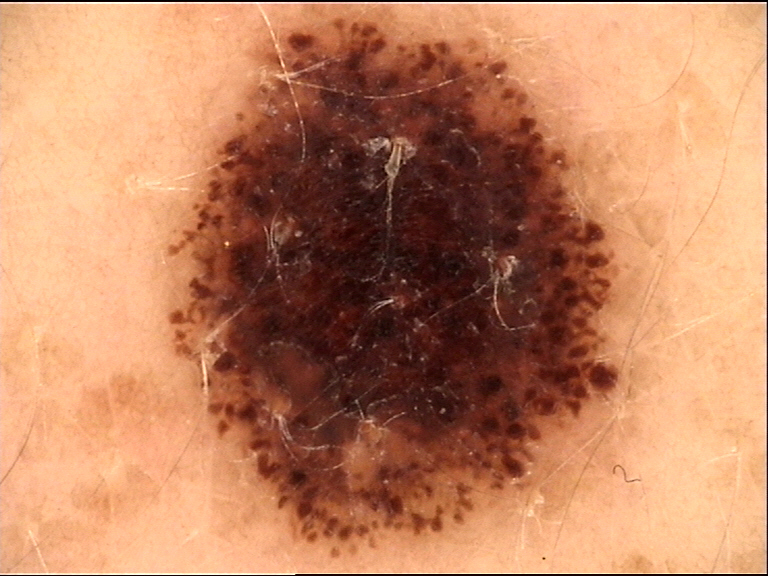Case: The architecture is that of a banal lesion. Impression: Consistent with a compound nevus.